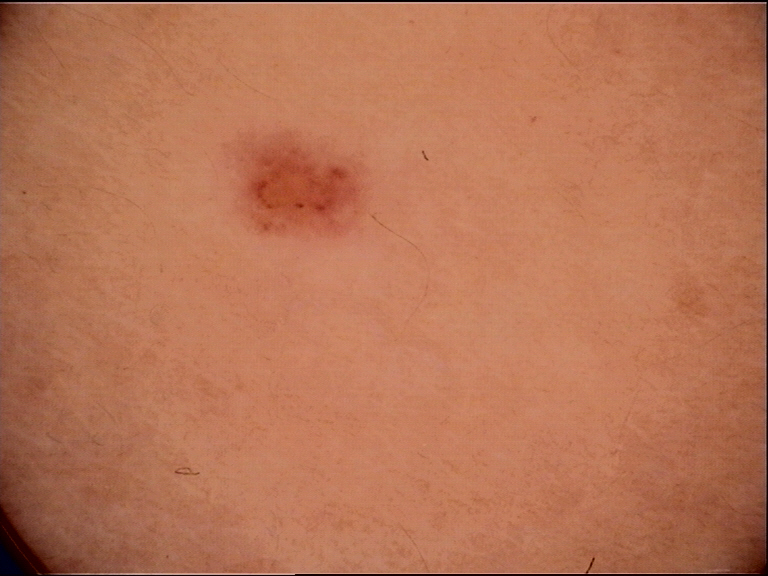A dermoscopic photograph of a skin lesion. Diagnosed as a dysplastic junctional nevus.